Dermoscopy of a skin lesion: 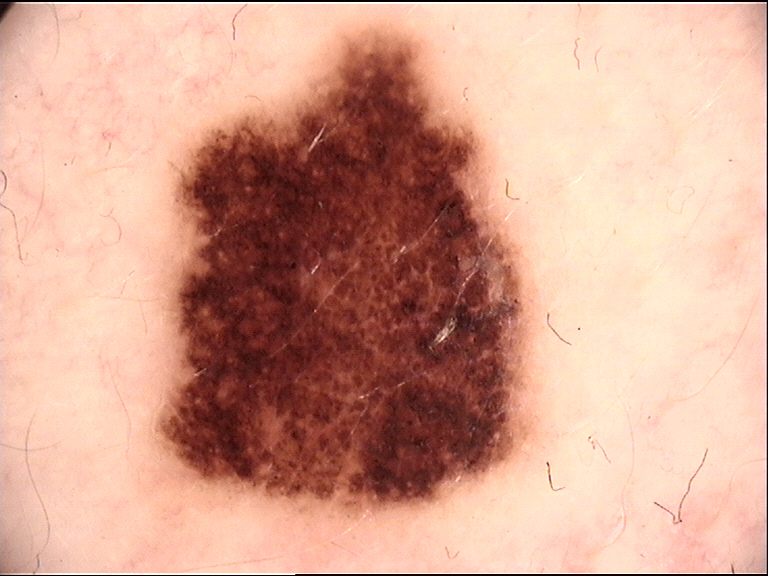Impression: The diagnostic label was a dysplastic compound nevus.